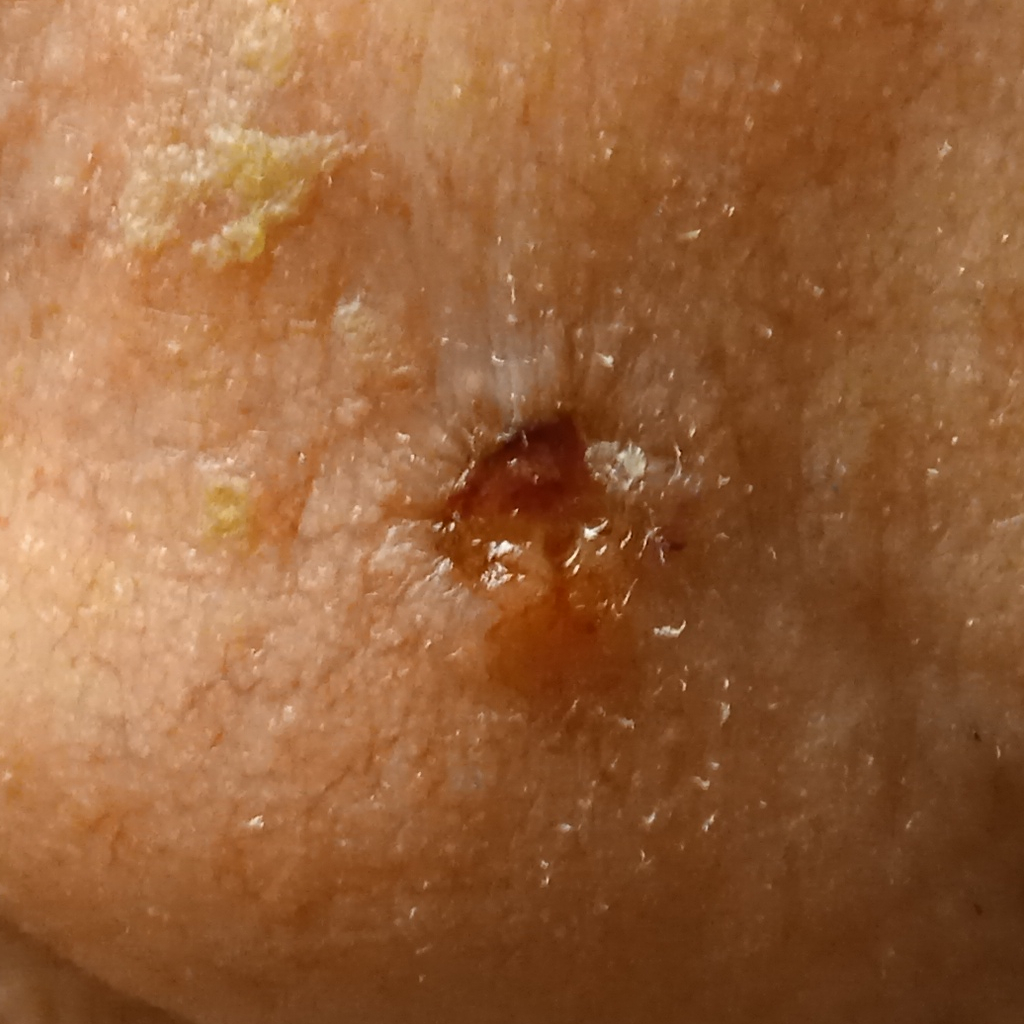Clinical context: A male subject 89 years of age. The referring clinician suspected basal cell carcinoma. Diagnosis: Histopathologically confirmed as a basal cell carcinoma, following excision, with a measured tumor thickness of 2.2 mm.